A clinical photograph of a skin lesion · per the chart, a prior melanoma · a female subject aged around 70 · the patient was assessed as skin type II: 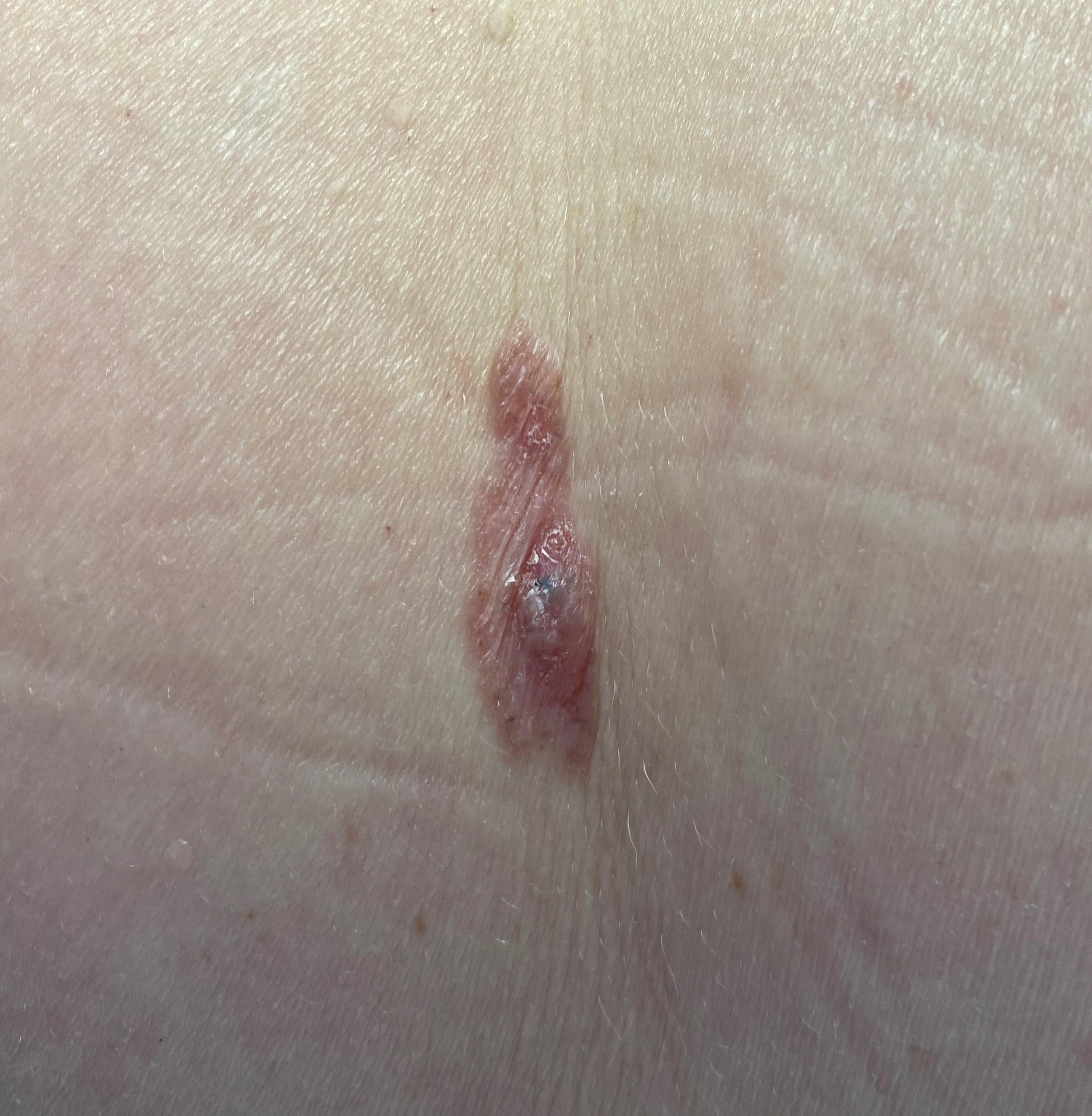Located on the trunk.
Biopsy-confirmed as a malignant lesion — a basal cell carcinoma.